A close-up photograph · the lesion involves the arm: 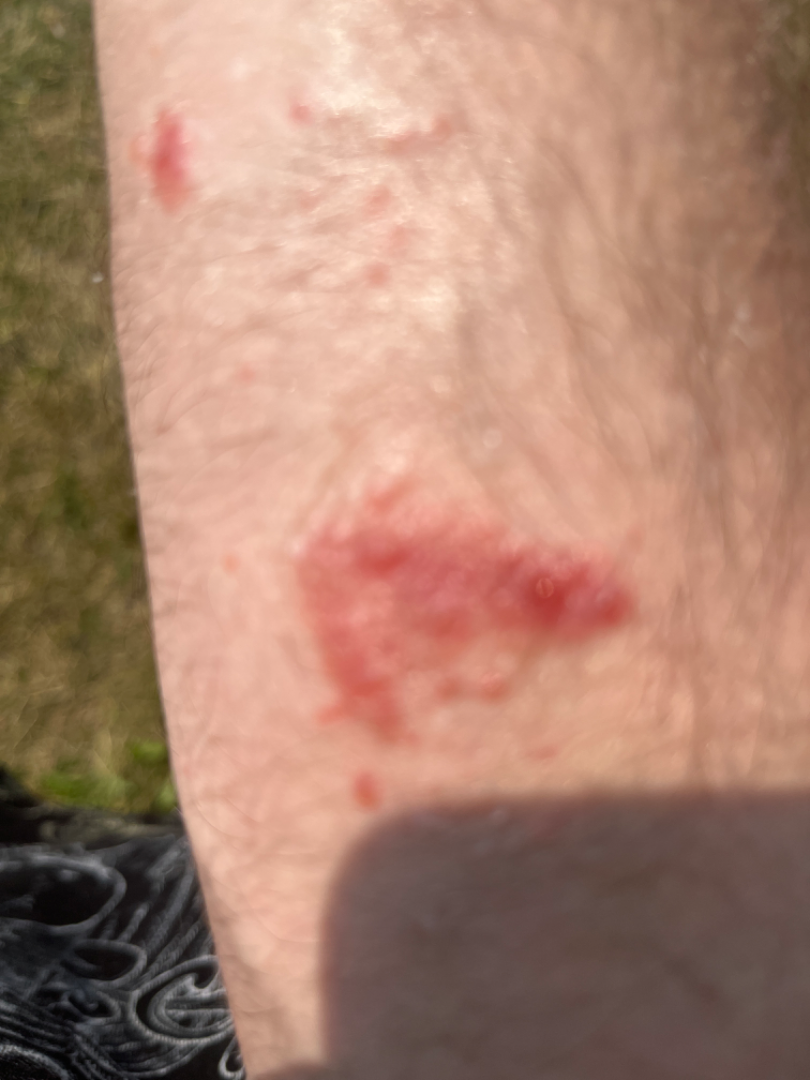The image was not sufficient for the reviewer to characterize the skin condition.